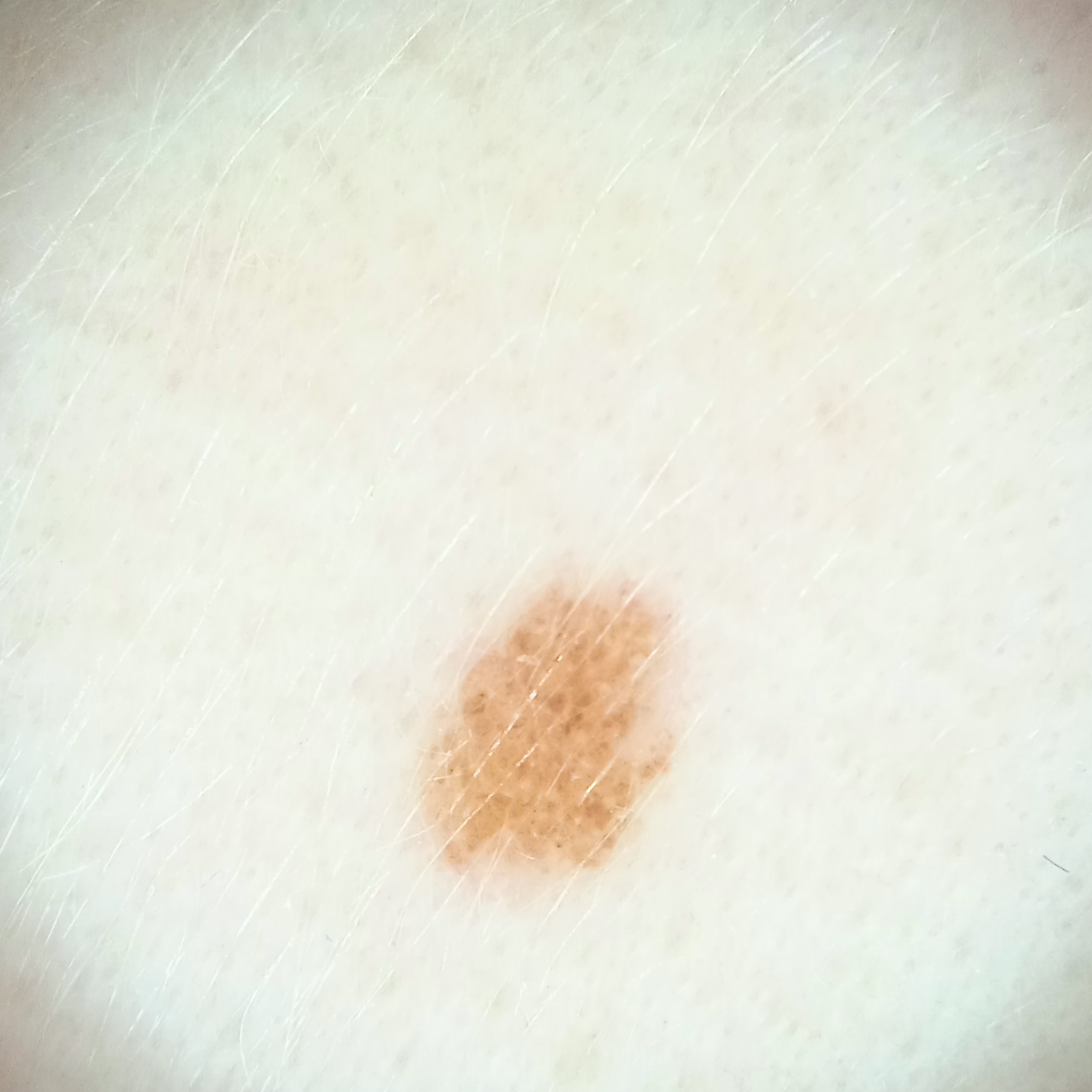nevus count: few melanocytic nevi overall | clinical context: research study (no referral diagnosis) | patient: female, aged 15 | sun reaction: skin reddens with sun exposure | image: dermoscopy | site: the face | diameter: 3.6 mm | diagnostic label: melanocytic nevus (dermatologist consensus).